A dermoscopy image of a single skin lesion · a male patient aged approximately 50.
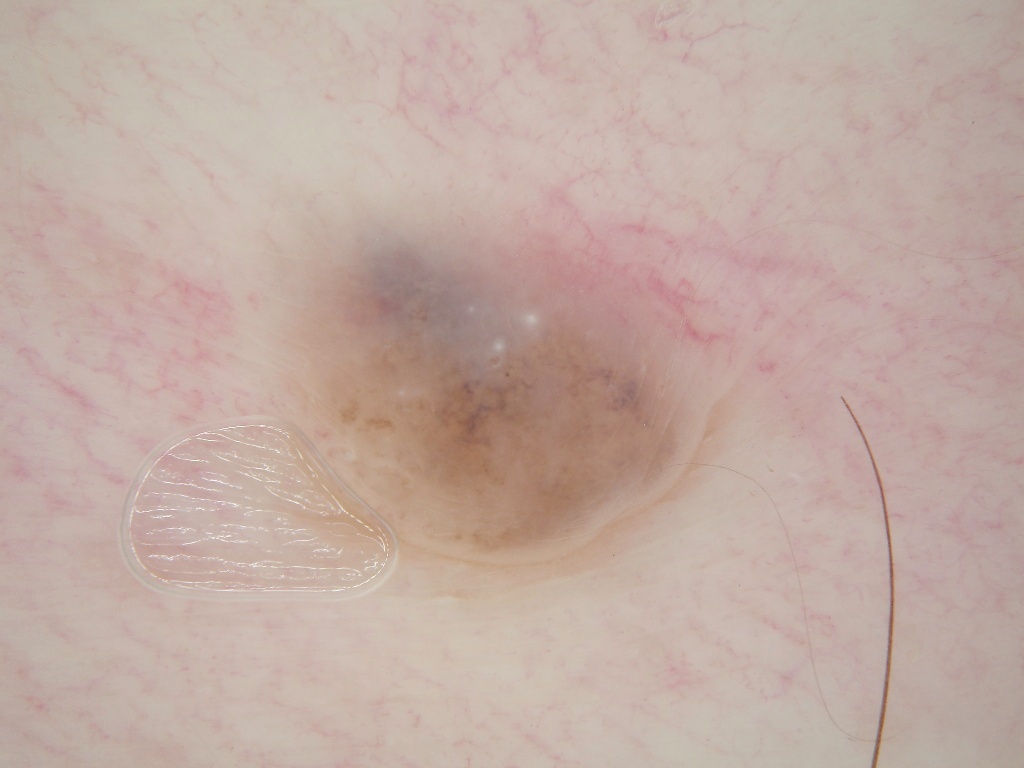Findings:
Dermoscopic assessment notes milia-like cysts. The lesion takes up about 15% of the image. In (x1, y1, x2, y2) order, the lesion is located at [254,214,717,564].
Assessment:
Expert review diagnosed this as a melanocytic nevus, a benign lesion.